The patient says their skin reddens painfully with sun exposure; a macroscopic clinical photograph of a skin lesion; a male patient age 65; acquired for a research image collection, with no referral diagnosis; the patient reports a family history of skin cancer, a personal history of skin cancer, and immunosuppression:
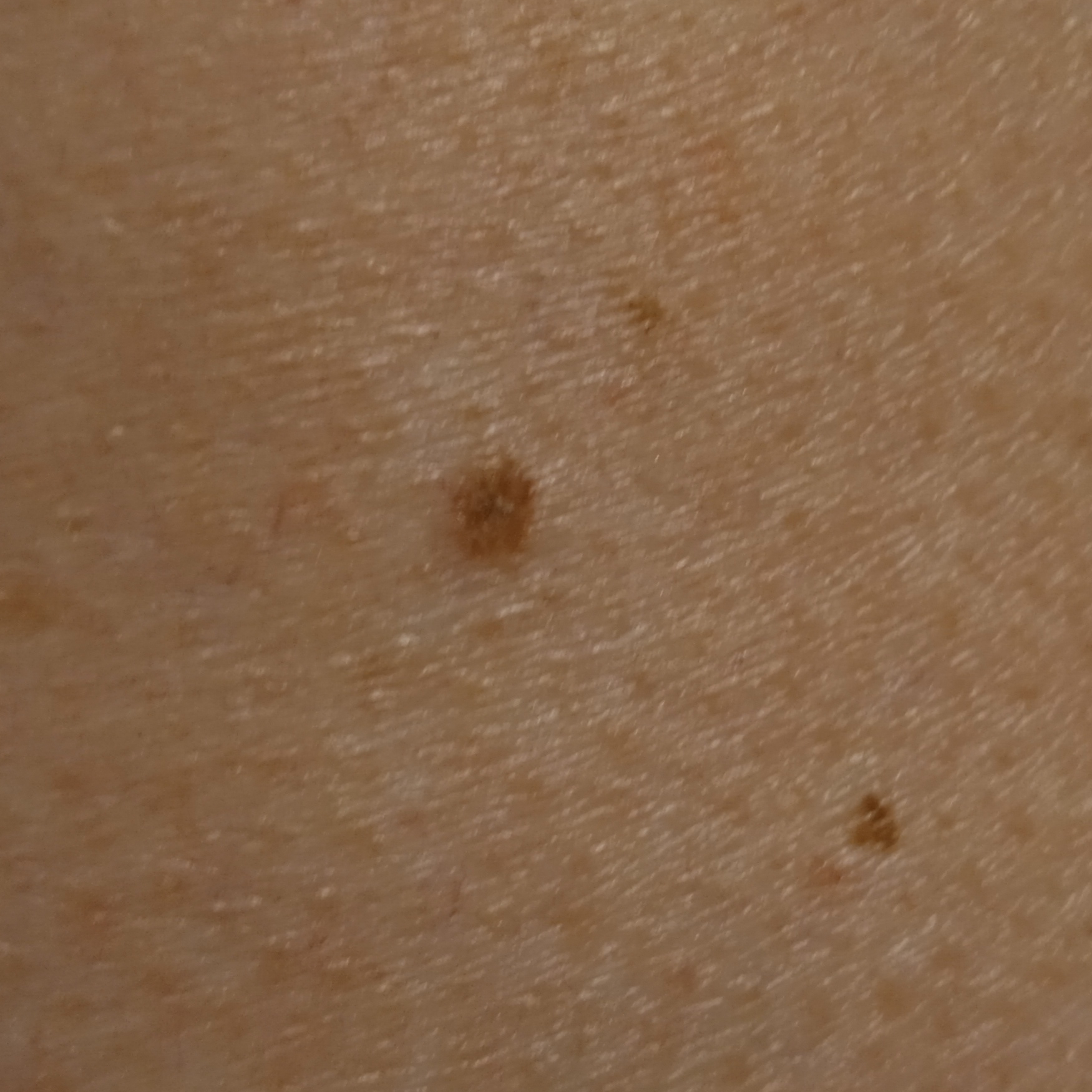size = 3.3 mm, diagnostic label = seborrheic keratosis (dermatologist consensus).